A male patient aged 58 to 62 · contact-polarized dermoscopy of a skin lesion.
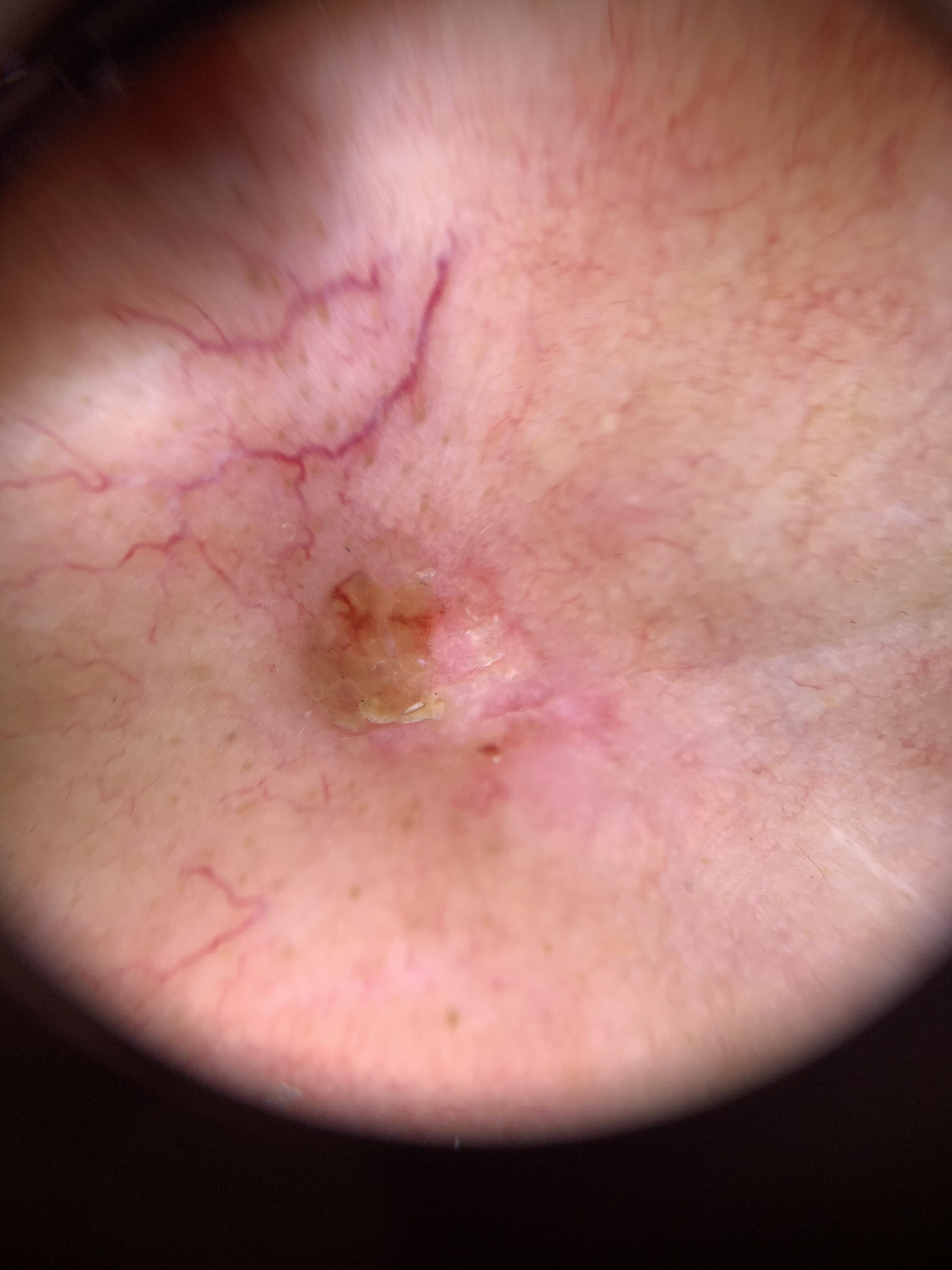The lesion was found on the head or neck. Biopsy-confirmed as a basal cell carcinoma.